The photo was captured at an angle; the patient notes the condition has been present for one to four weeks; the patient notes associated joint pain; the patient considered this a hair problem; the head or neck is involved; reported lesion symptoms include bothersome appearance:
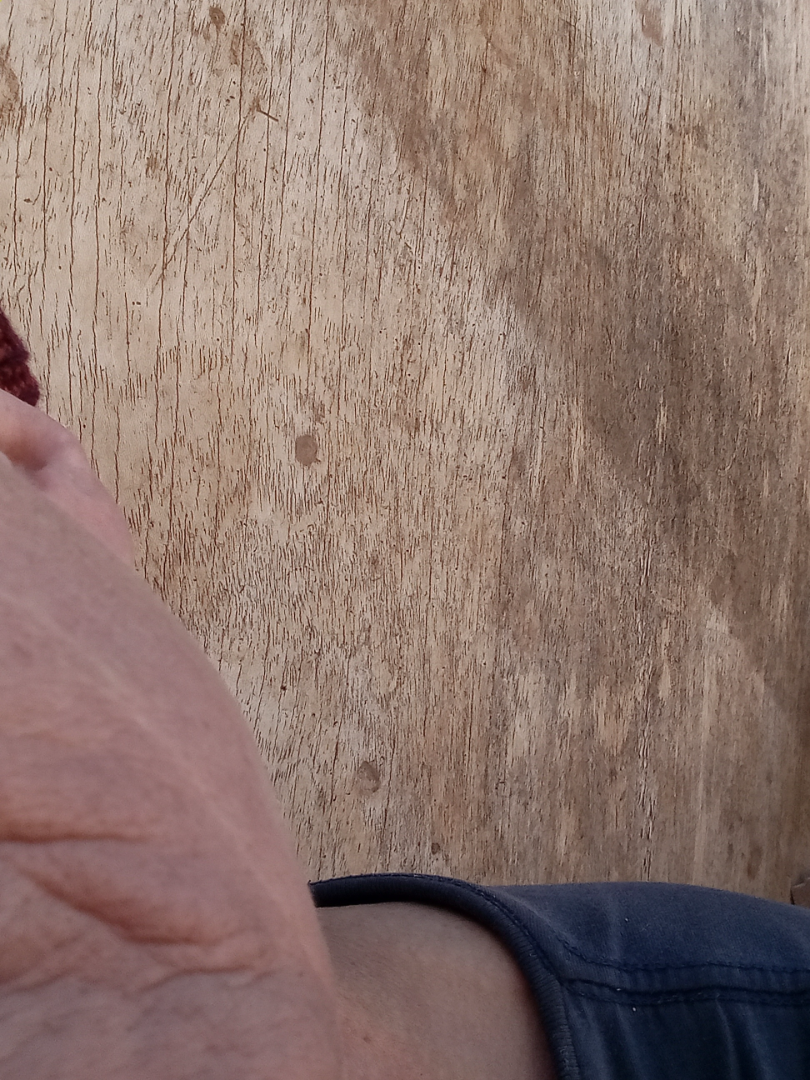Review: No discernible skin pathology was identified on dermatologist review.